A female subject in their mid-80s or older — 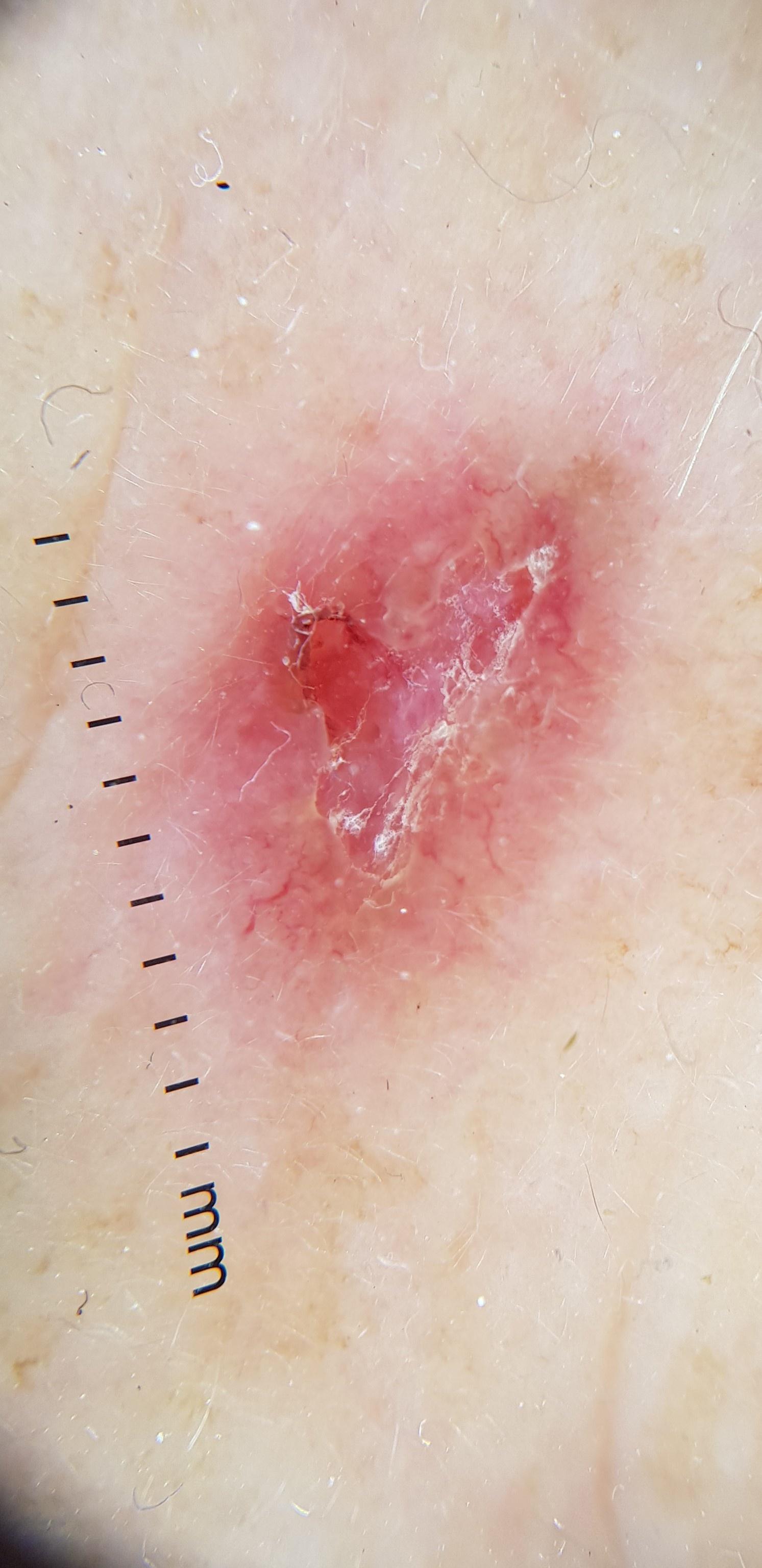Located on the head or neck. The biopsy diagnosis was a basal cell carcinoma.